A dermoscopic close-up of a skin lesion.
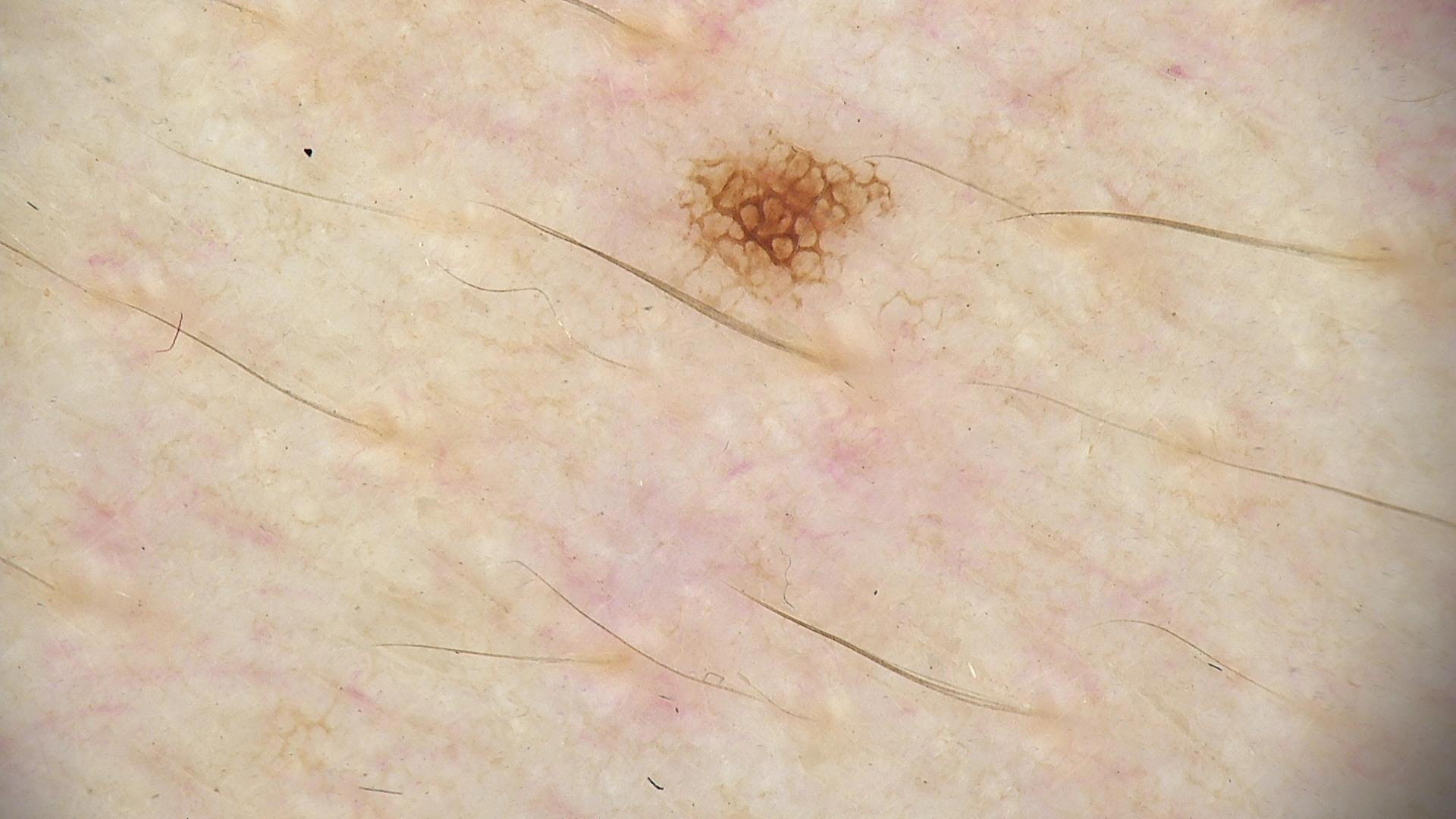The diagnostic label was a benign lesion — a dysplastic junctional nevus.